A skin lesion imaged with a dermatoscope, a male patient aged approximately 25 — 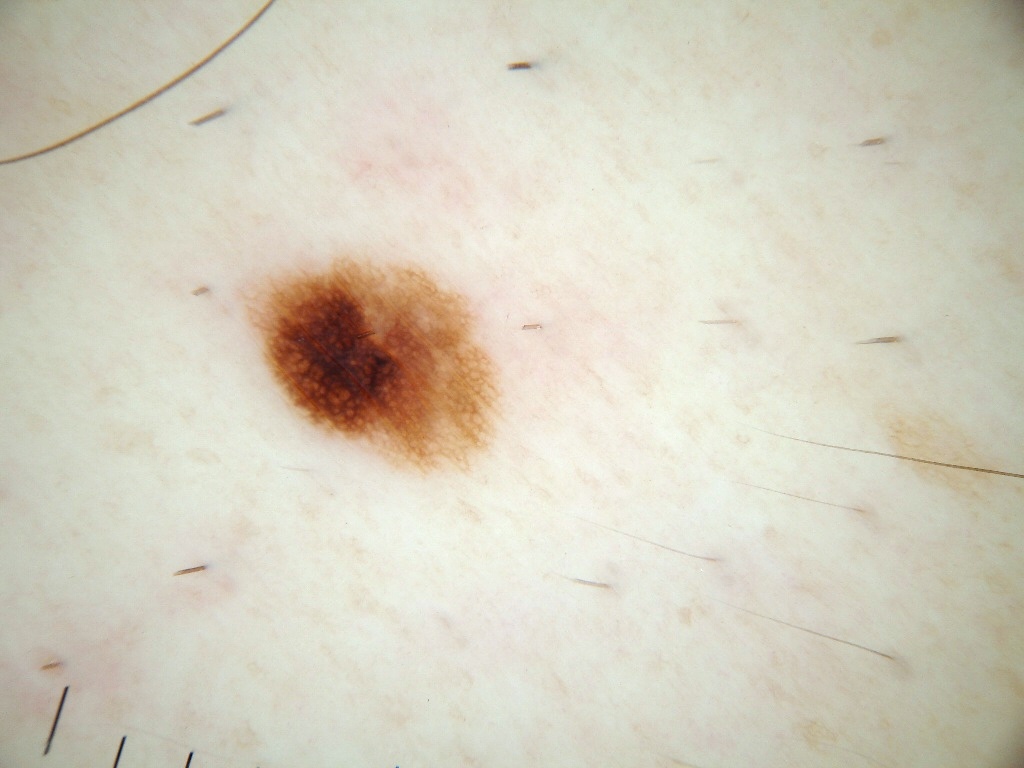<case>
<lesion_location>
  <bbox_xyxy>239, 254, 495, 469</bbox_xyxy>
</lesion_location>
<dermoscopic_features>
  <present>pigment network</present>
  <absent>negative network, milia-like cysts, streaks, globules</absent>
</dermoscopic_features>
<diagnosis>
  <name>melanocytic nevus</name>
  <malignancy>benign</malignancy>
  <lineage>melanocytic</lineage>
  <provenance>clinical</provenance>
</diagnosis>
</case>